A smartphone photograph of a skin lesion; a patient in their late 50s:
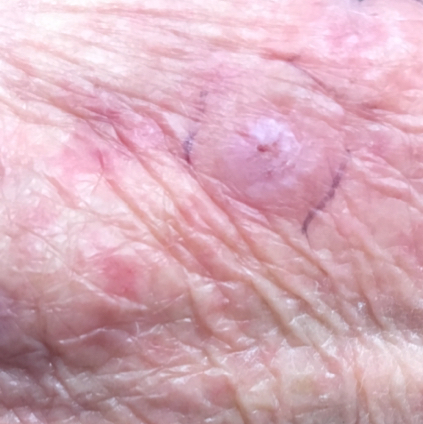The diagnostic impression was an actinic keratosis.